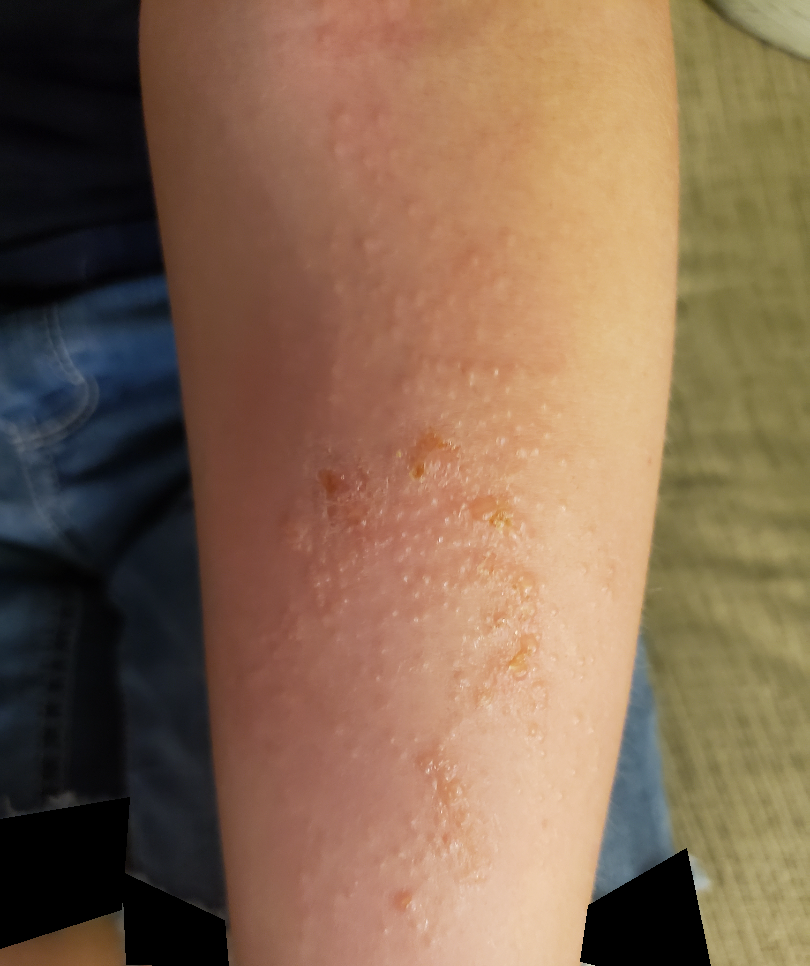Q: What is the differential diagnosis?
A: Allergic Contact Dermatitis (leading); Impetigo (considered)